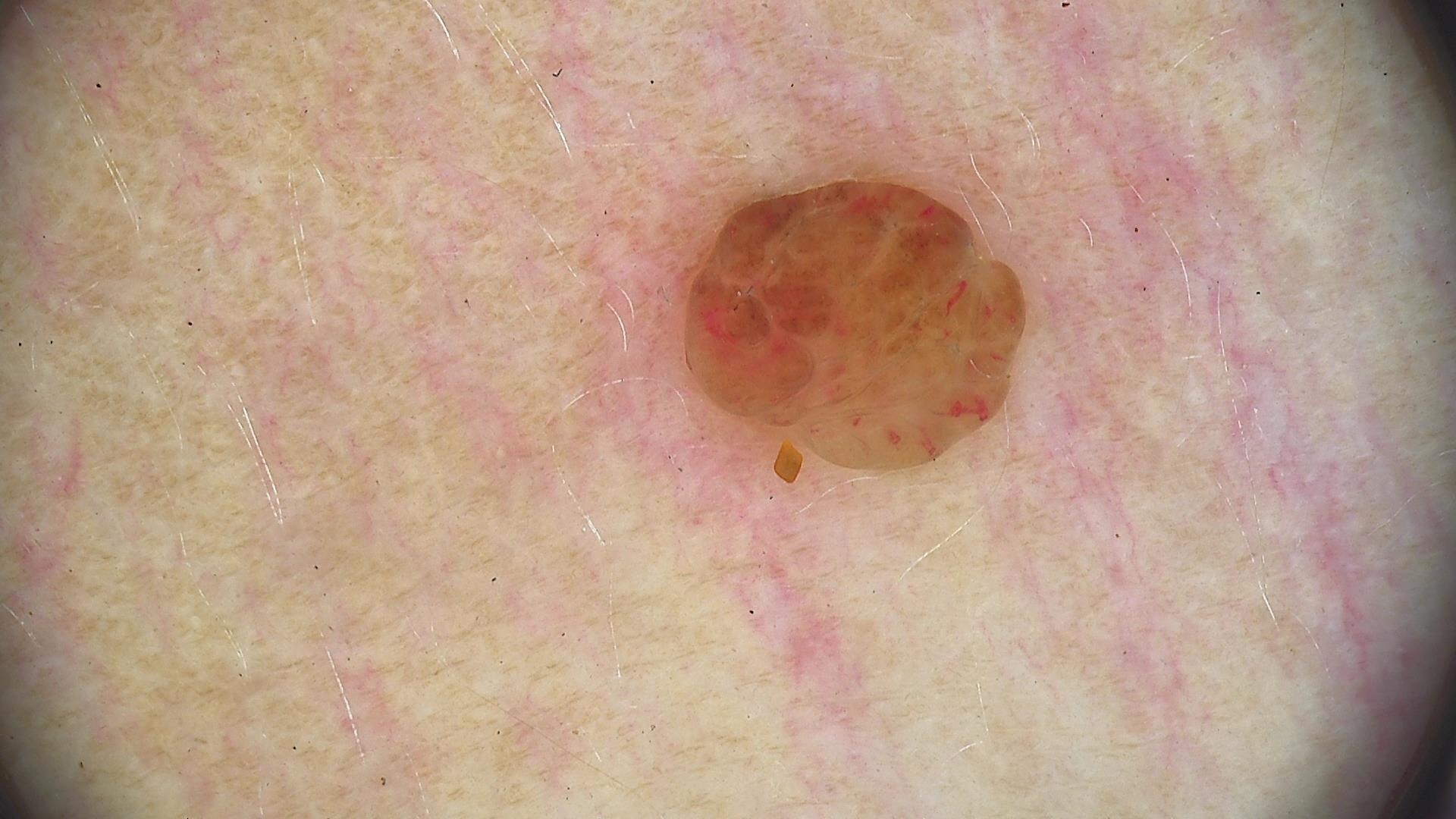A dermoscopy image of a single skin lesion. This is a banal lesion. The diagnostic label was a dermal nevus.